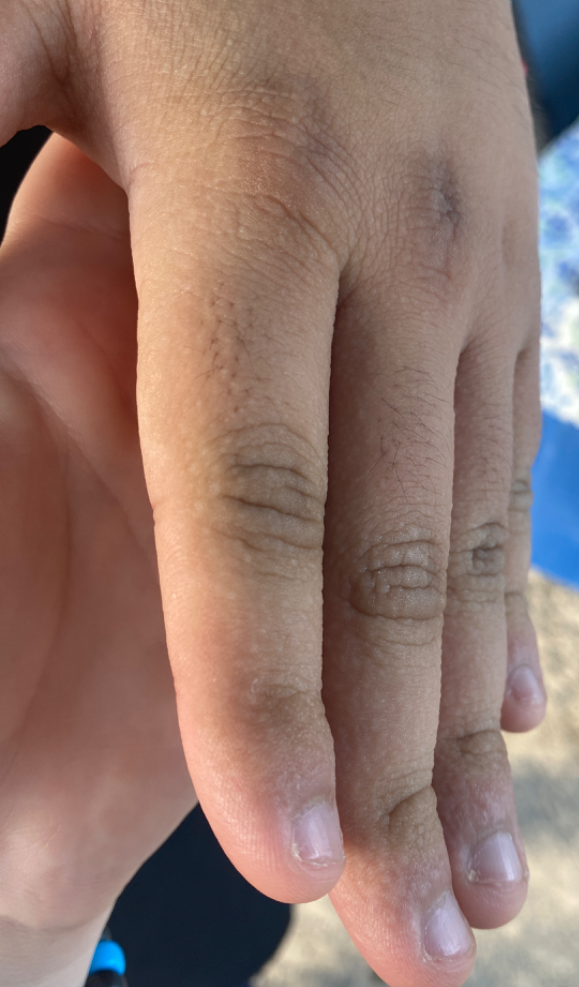photo taken: at an angle
skin tone: non-clinician graders estimated Monk Skin Tone 6 (US pool) or 4 (India pool)
assessment: the favored diagnosis is Acrokeratosis verruciformis